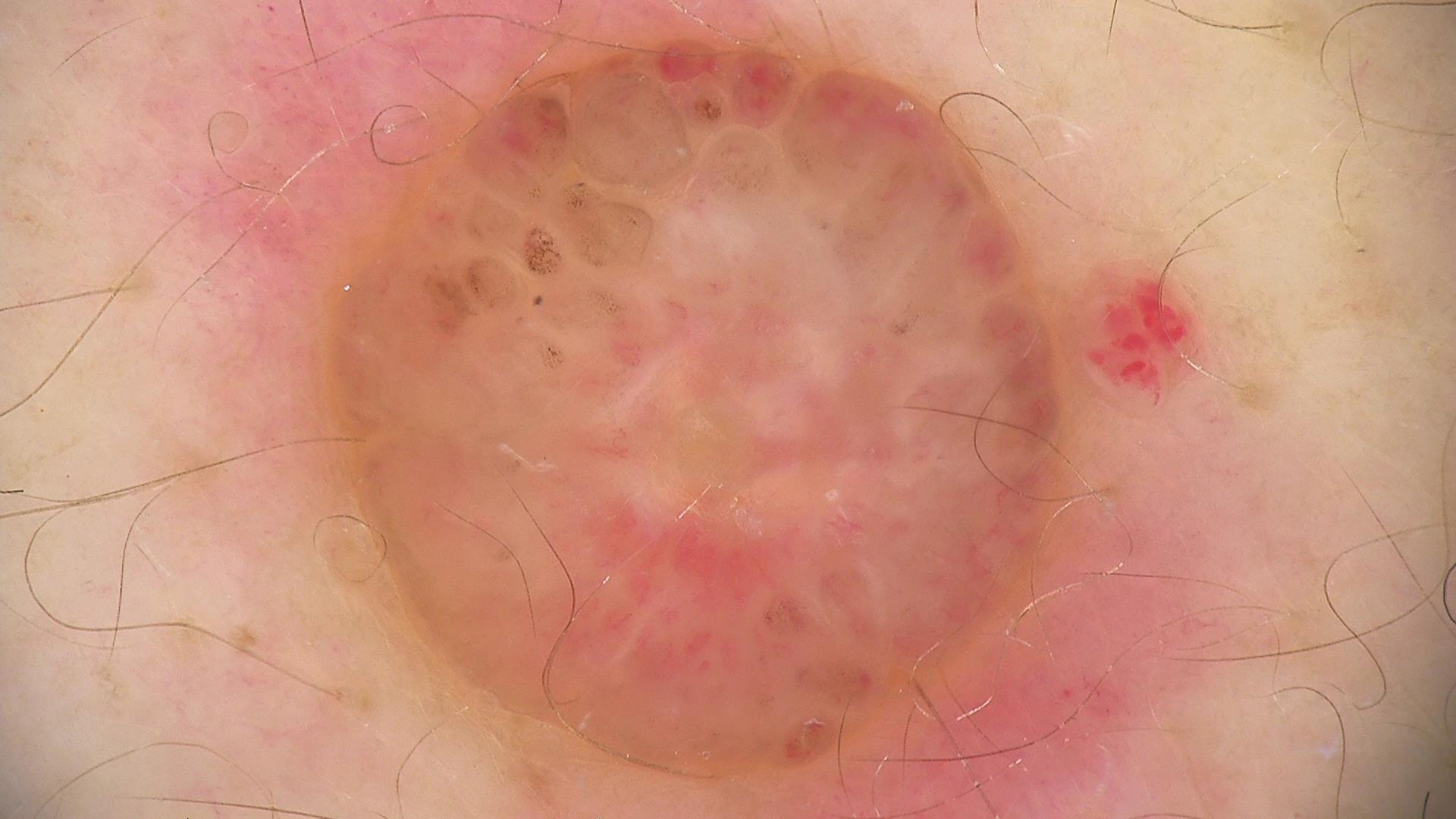A dermoscopic image of a skin lesion. Labeled as a banal lesion — a dermal nevus.